The subject is a female aged 18–29 · located on the back of the hand and top or side of the foot · this image was taken at an angle — 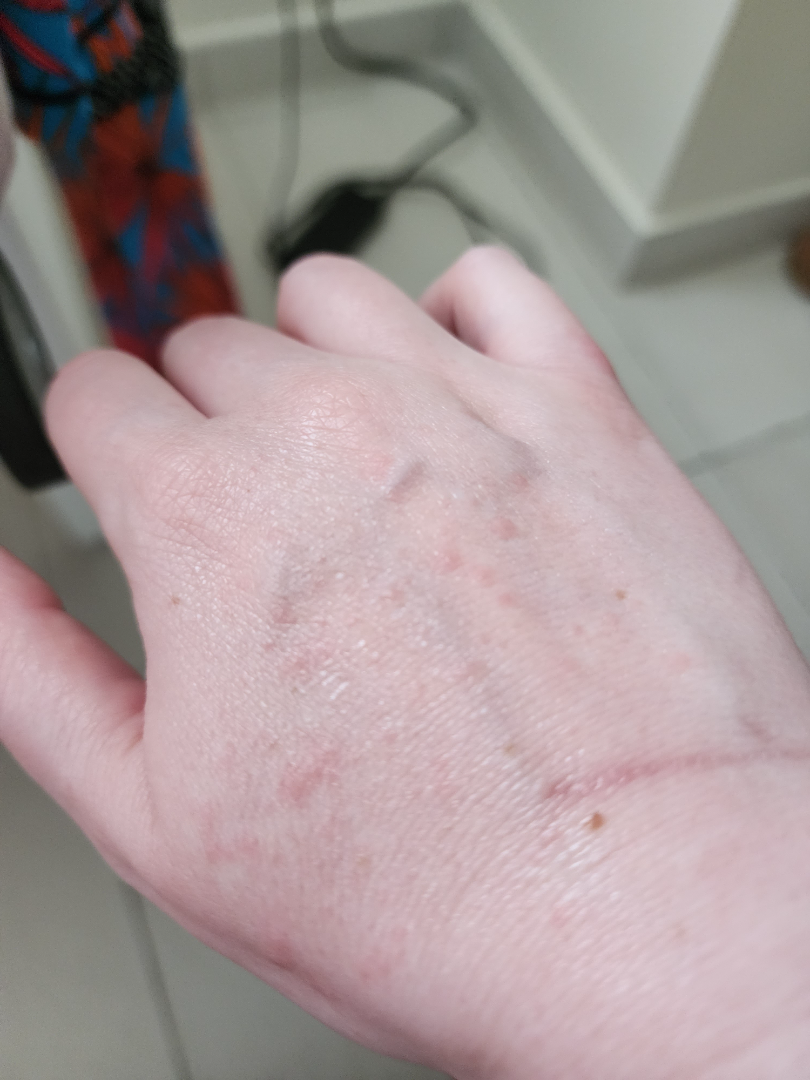Case summary:
* assessment · indeterminate